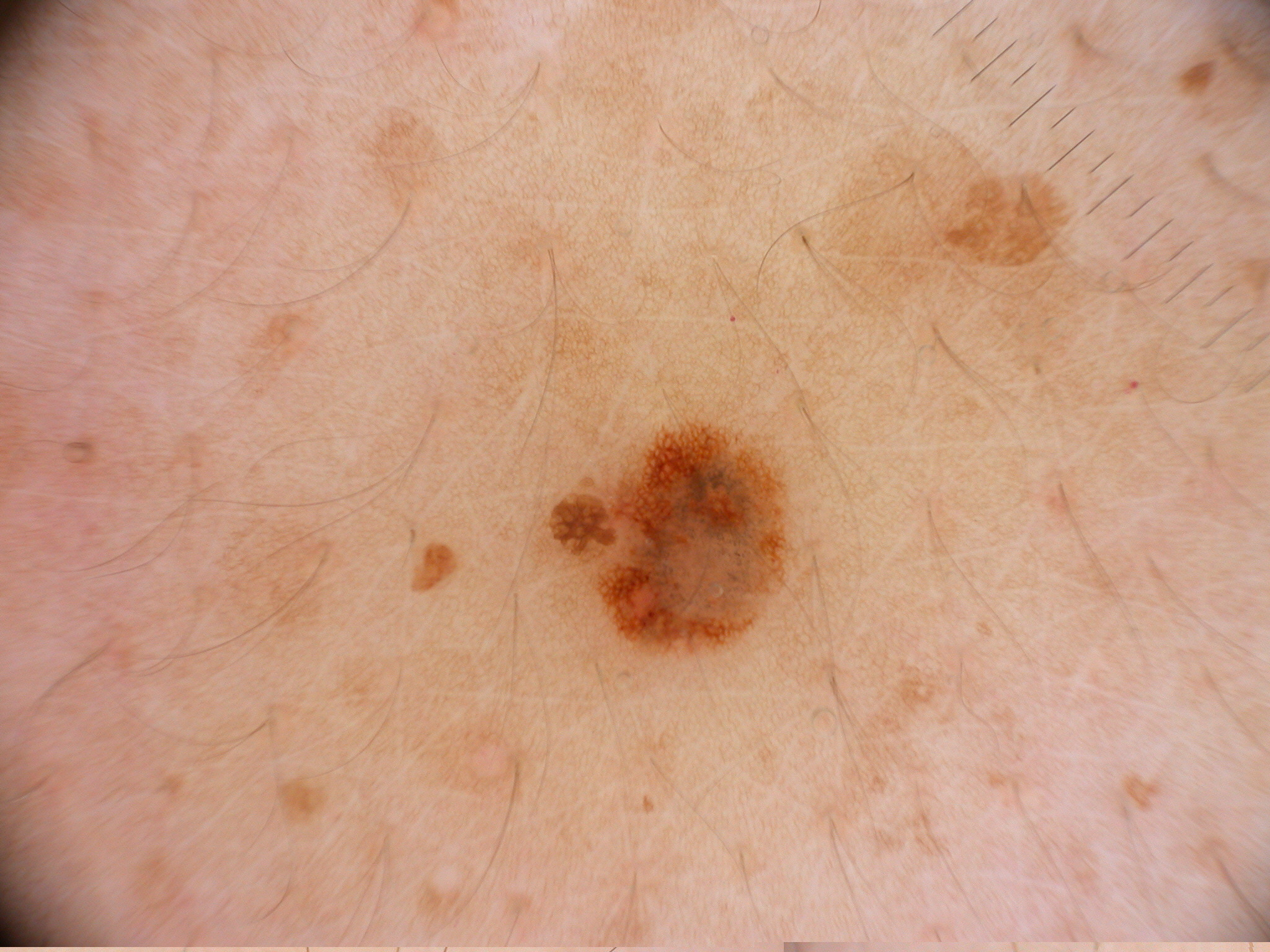<lesion>
<image>
  <modality>dermoscopy</modality>
</image>
<lesion_location>
  <bbox_xyxy>591, 418, 793, 659</bbox_xyxy>
</lesion_location>
<diagnosis>
  <malignancy>benign</malignancy>
  <provenance>clinical</provenance>
</diagnosis>
</lesion>